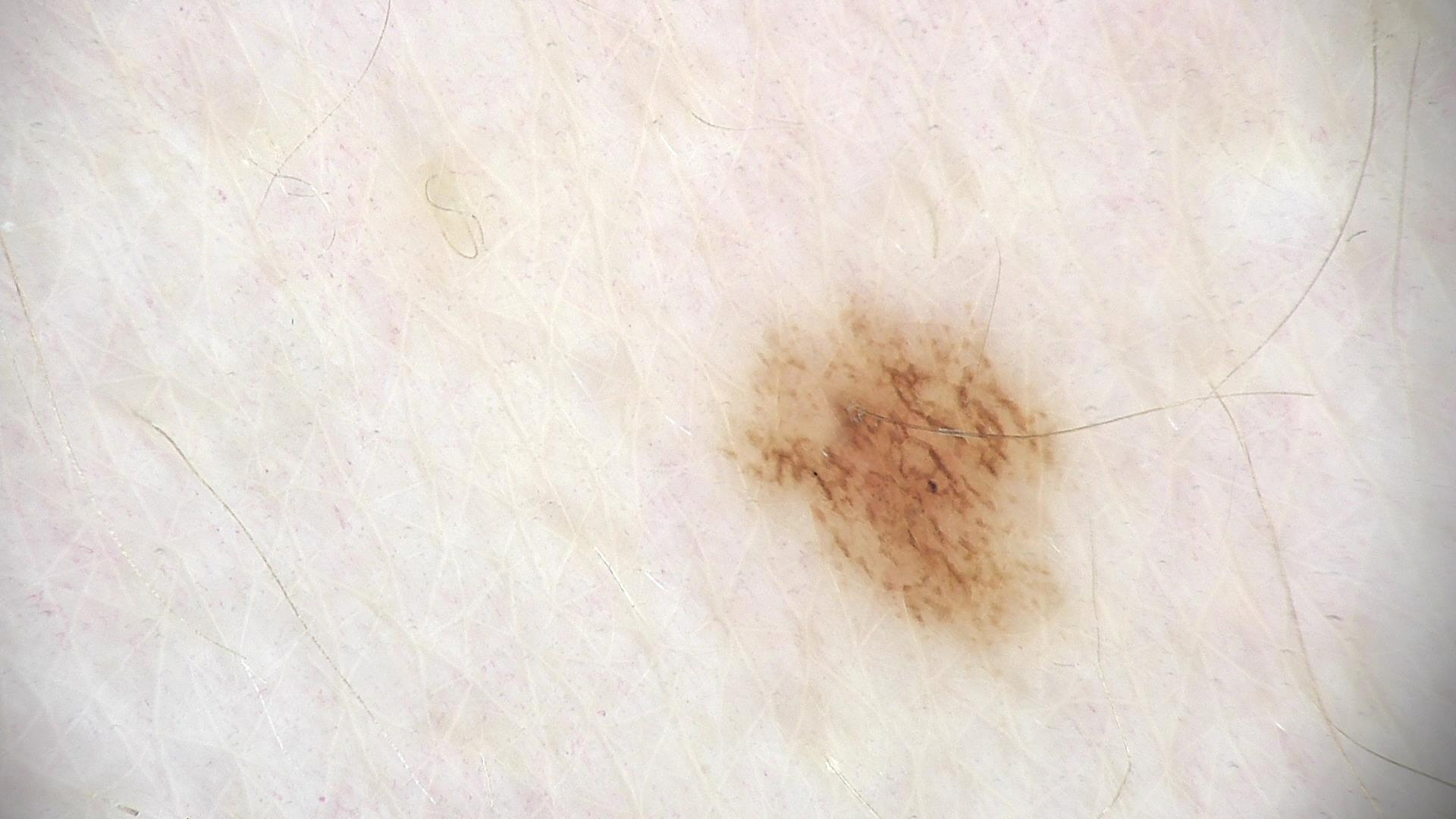Dermoscopy of a skin lesion. The diagnostic label was a benign lesion — a dysplastic junctional nevus.